The patient considered this a rash; this image was taken at an angle; female patient, age 18–29; skin tone: Fitzpatrick skin type I; located on the arm, leg and front of the torso:
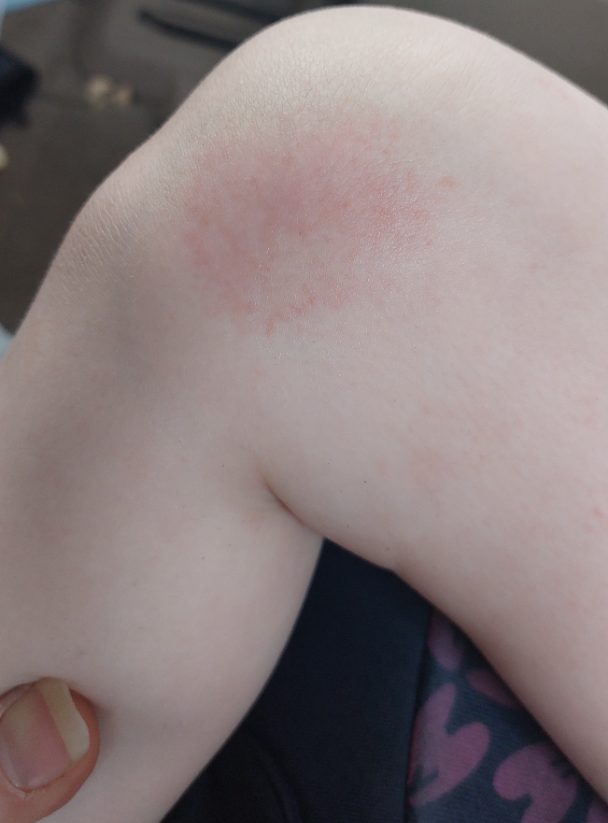Review:
The dermatologist could not determine a likely condition from the photograph alone.